A male subject aged 73-77 · a dermoscopy image of a single skin lesion:
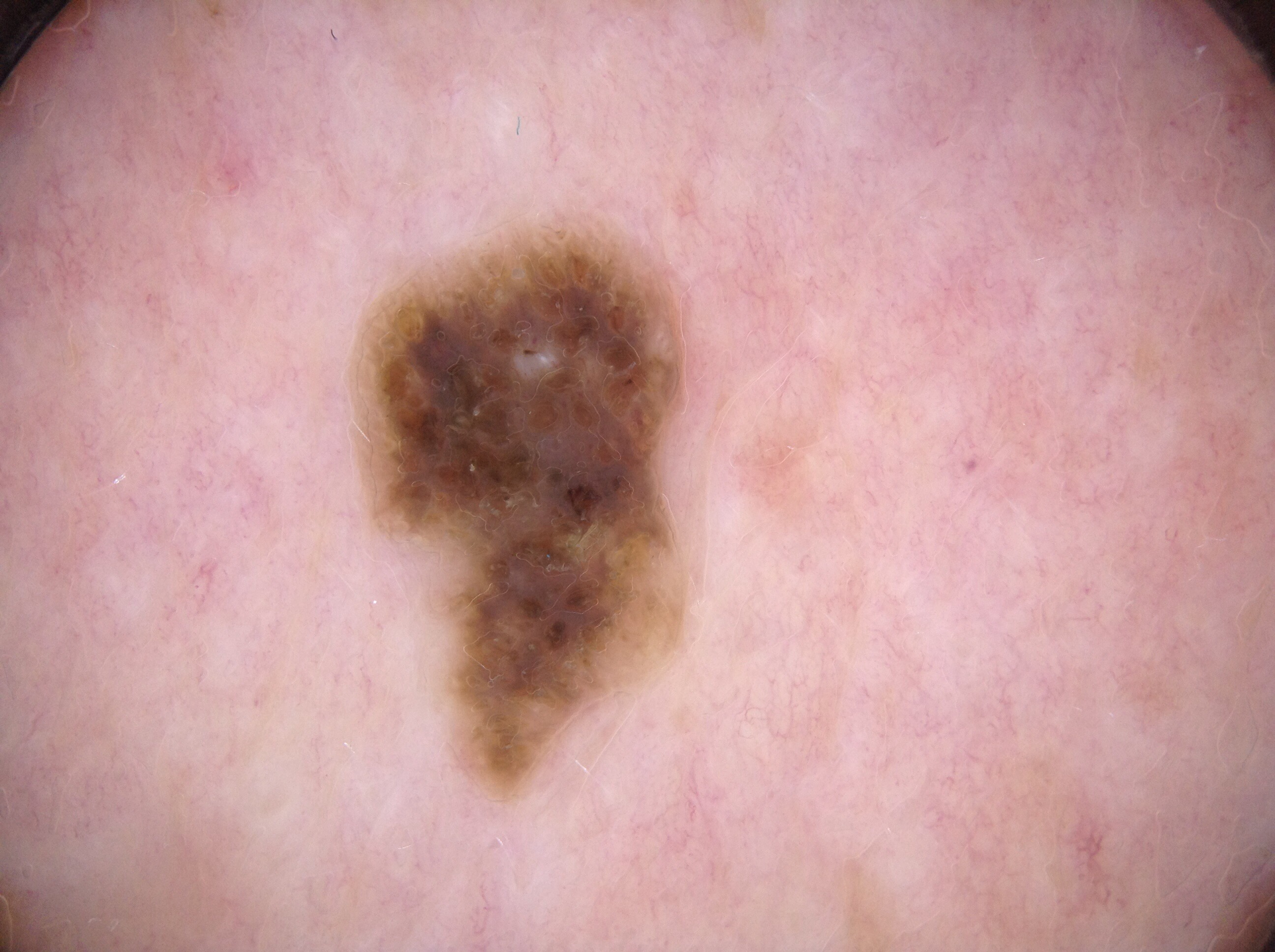Dermoscopic assessment notes milia-like cysts; no streaks, negative network, or pigment network.
With coordinates (x1, y1, x2, y2), the lesion's extent is [369,231,687,781].
Consistent with a seborrheic keratosis, a benign skin lesion.